A male patient, aged 58 to 62. A dermatoscopic image of a skin lesion — 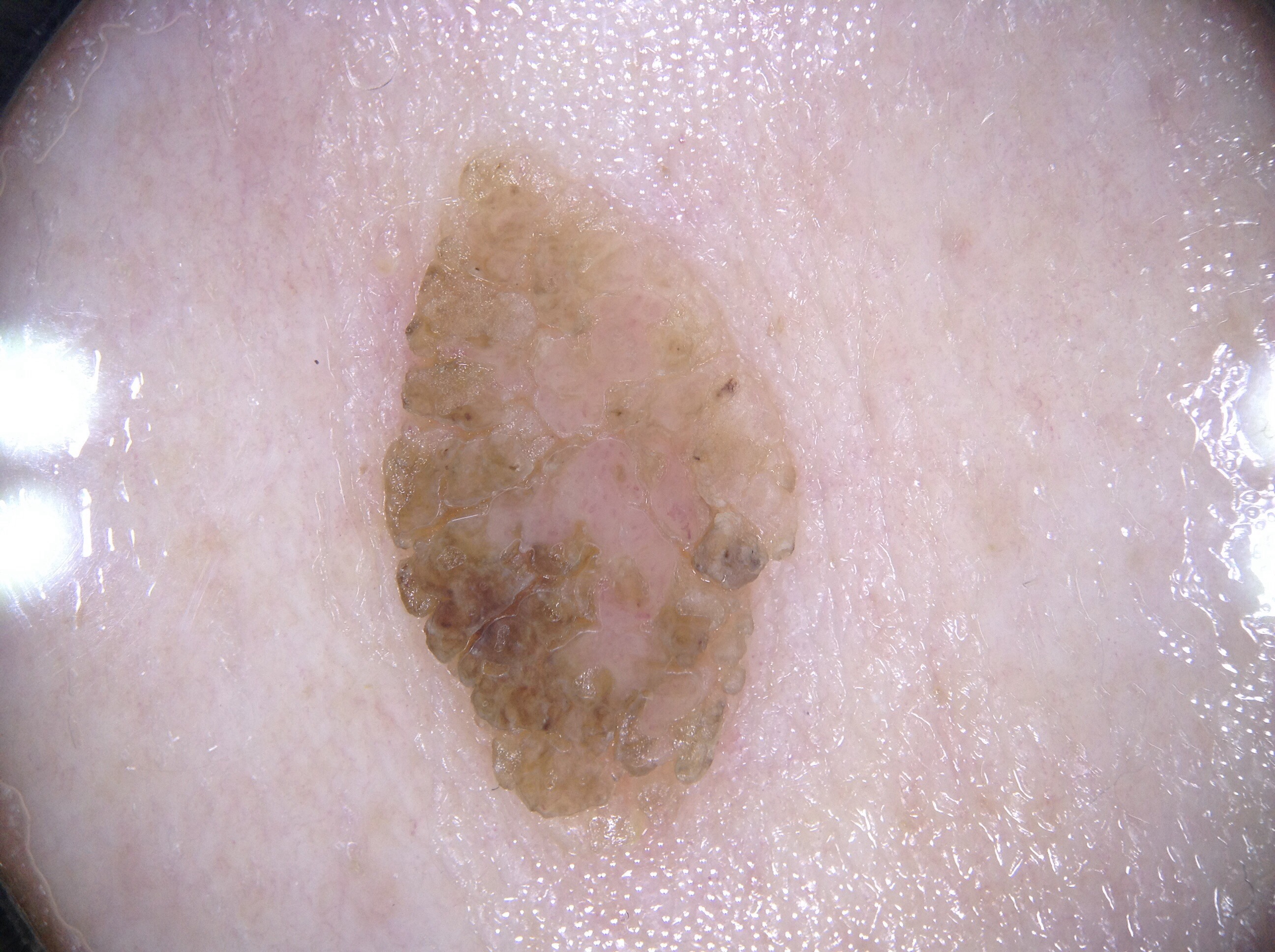Summary: As (left, top, right, bottom), the visible lesion spans [369, 156, 797, 825]. A mid-sized lesion within the field. Dermoscopically, the lesion shows no milia-like cysts, pigment network, streaks, or negative network. Impression: Diagnosed as a seborrheic keratosis, a benign skin lesion.